A female patient approximately 25 years of age; a dermoscopic close-up of a skin lesion — 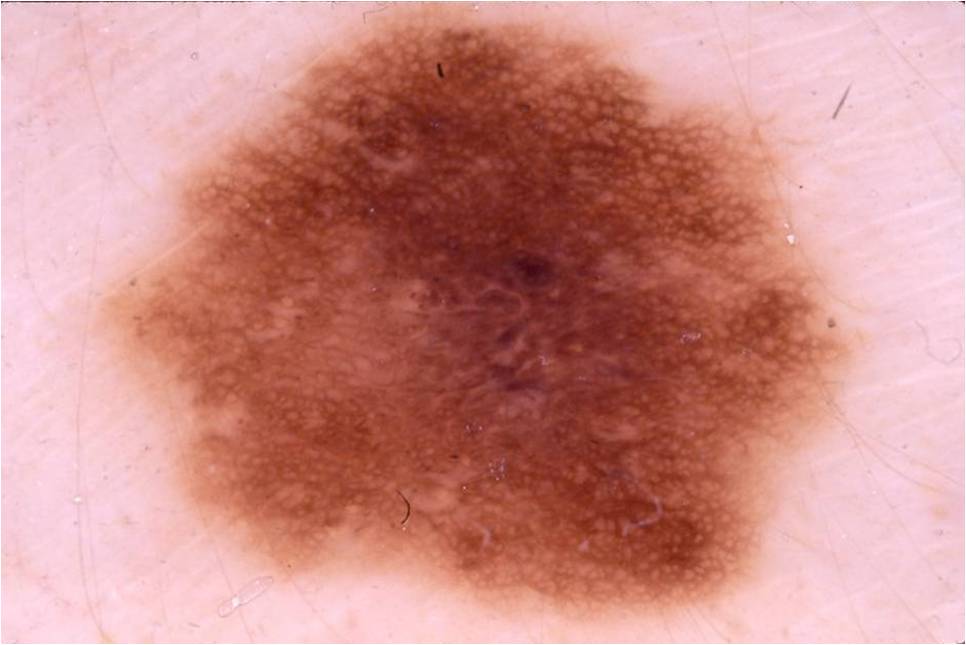Case summary: As (left, top, right, bottom), the visible lesion spans 106, 0, 846, 613. On dermoscopy, the lesion shows pigment network and negative network; no streaks, milia-like cysts, or globules. Impression: Clinically diagnosed as a melanocytic nevus.